Female patient, age 40–49. The lesion is described as rough or flaky and raised or bumpy. The condition has been present for less than one week. The affected area is the arm. The contributor reports itching. An image taken at a distance.
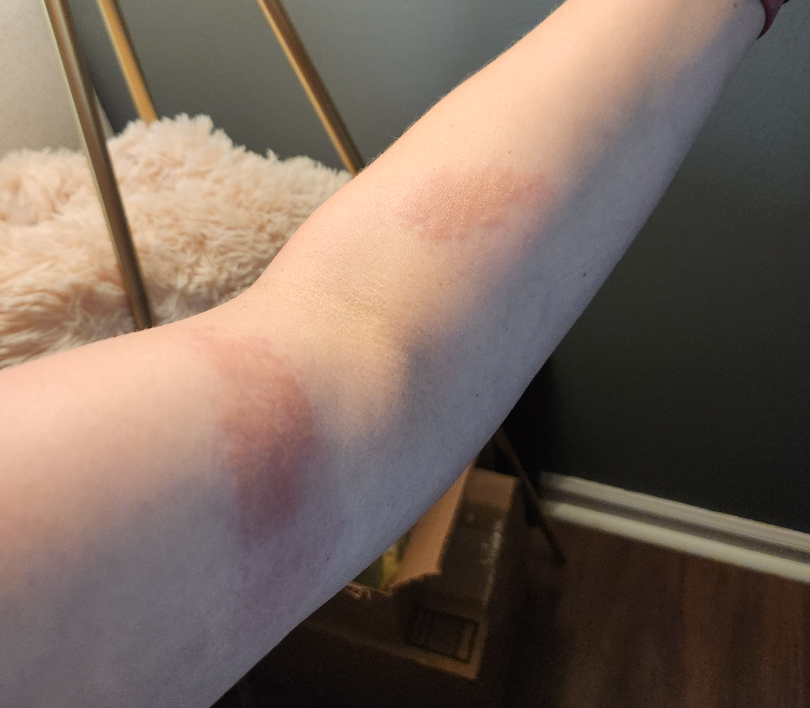Case summary:
– dermatologist impression: Photodermatitis and Acute and chronic dermatitis were each considered, in no particular order